Texture is reported as fluid-filled and raised or bumpy, the lesion involves the arm and leg, self-categorized by the patient as a rash, an image taken at an angle, no constitutional symptoms were reported, Fitzpatrick skin type III; lay reviewers estimated Monk Skin Tone 3:
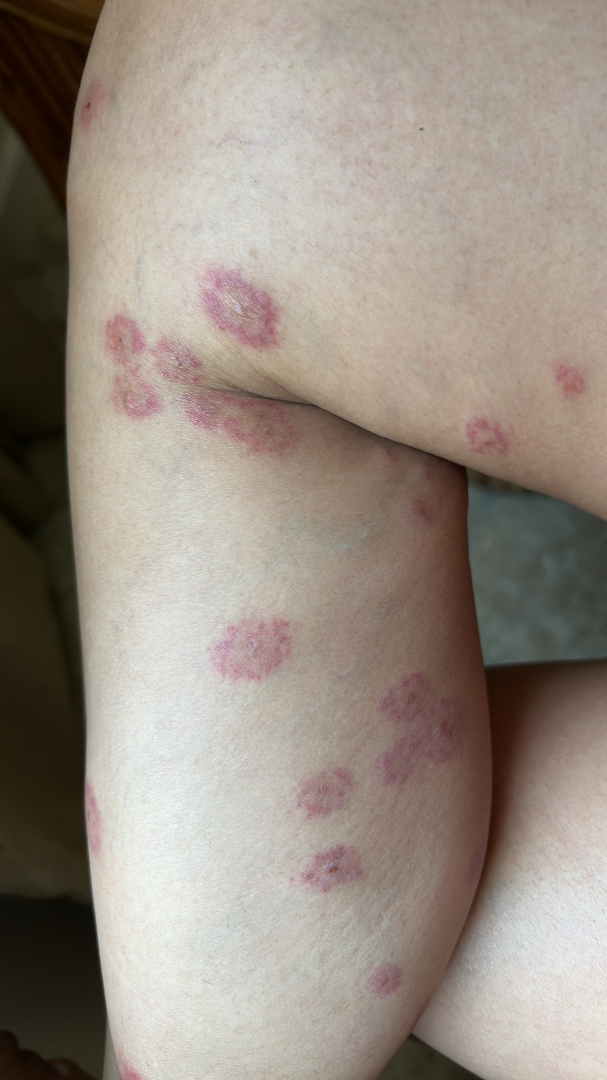The reviewing dermatologists' impression was: Erythema multiforme (primary); Insect Bite (possible); Leukocytoclastic Vasculitis (unlikely); Drug Rash (unlikely).